A dermoscopy image of a single skin lesion.
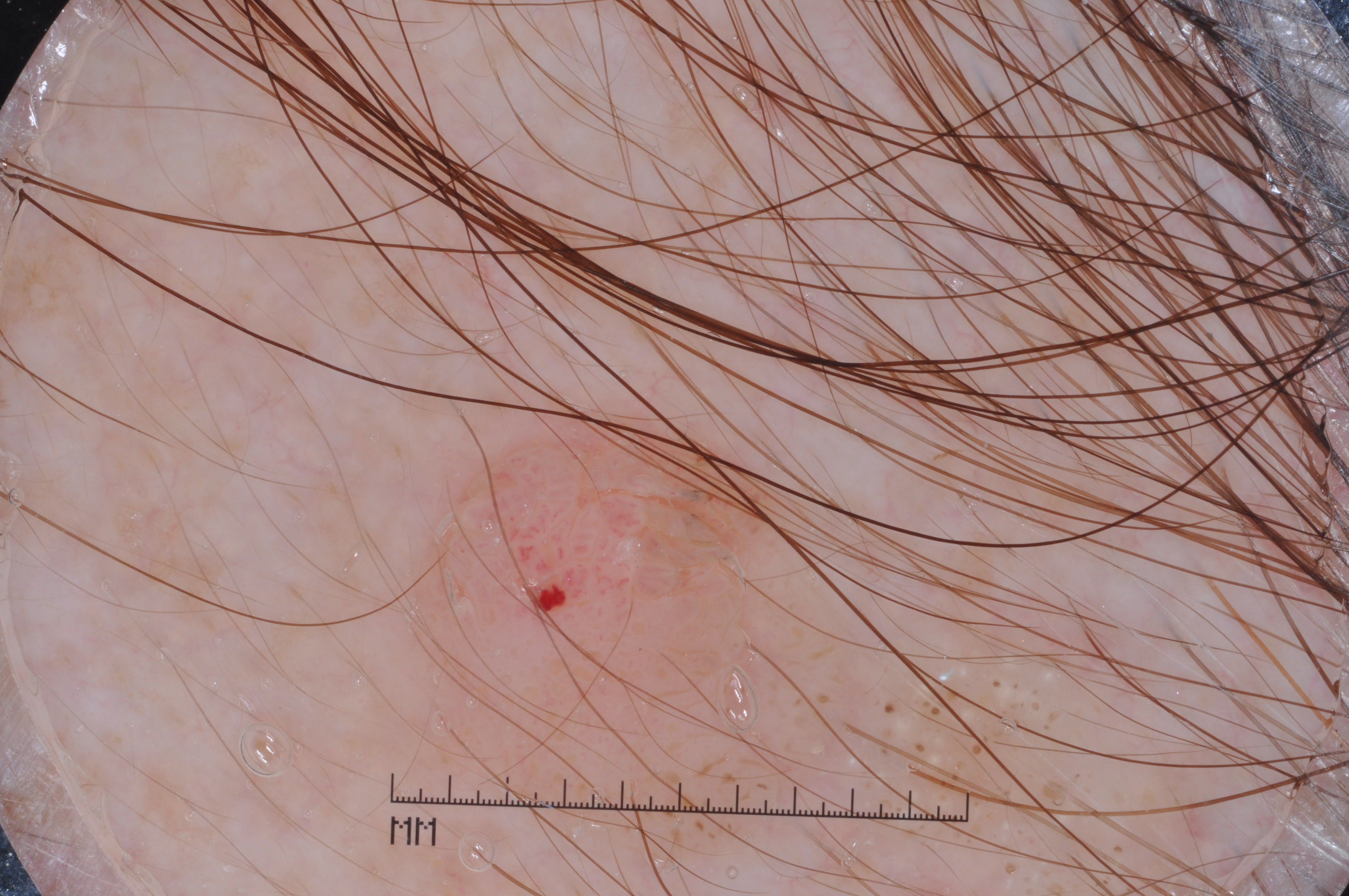Summary:
On dermoscopy, the lesion shows milia-like cysts; no streaks, pigment network, or negative network. As (left, top, right, bottom), the lesion's extent is [422,385,822,644].
Conclusion:
Clinically diagnosed as a seborrheic keratosis, a lesion of keratinocytic origin.